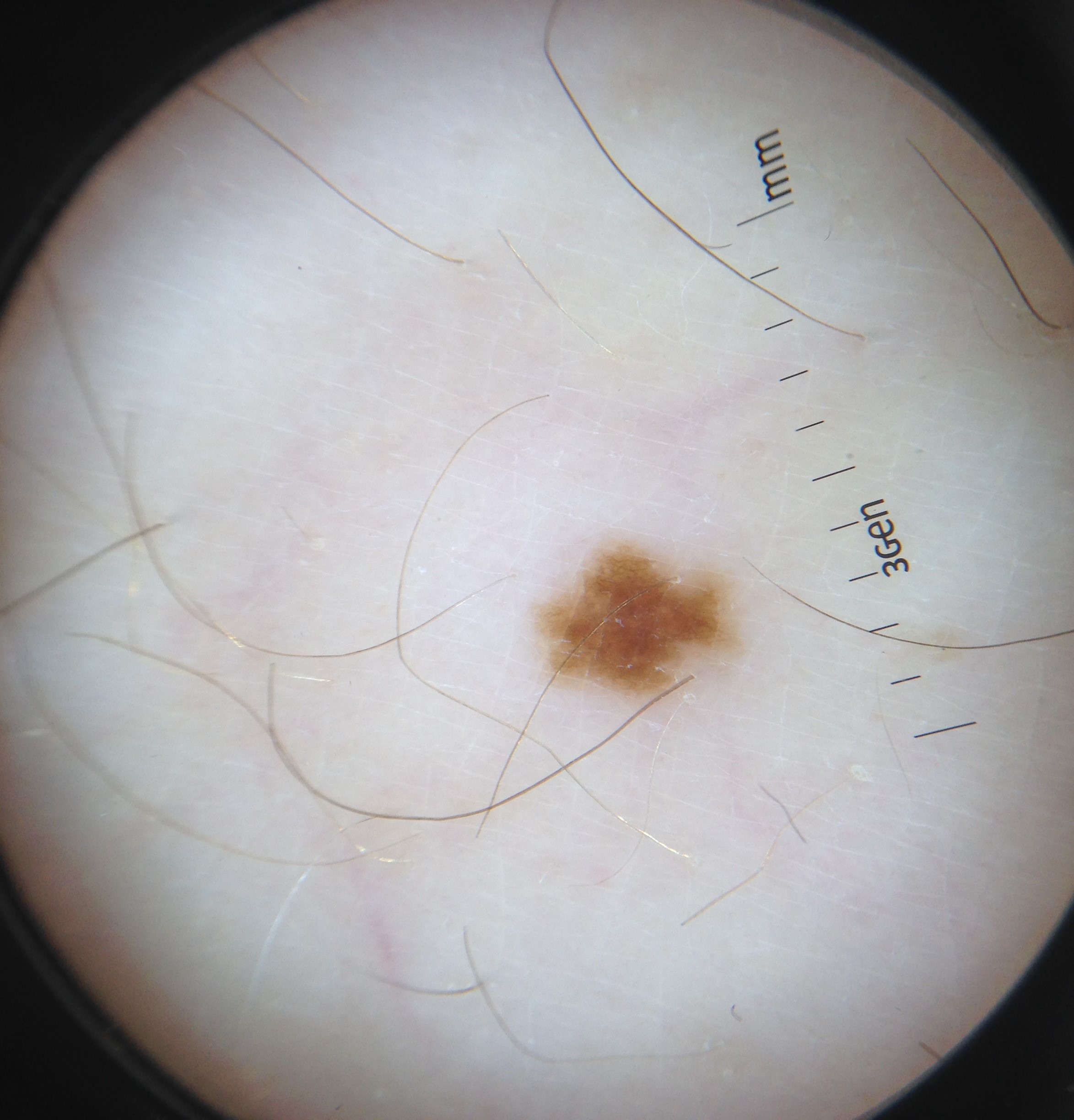A dermoscopic image of a skin lesion.
The morphology is that of a banal lesion.
The diagnostic label was a junctional nevus.